A dermoscopic image of a skin lesion.
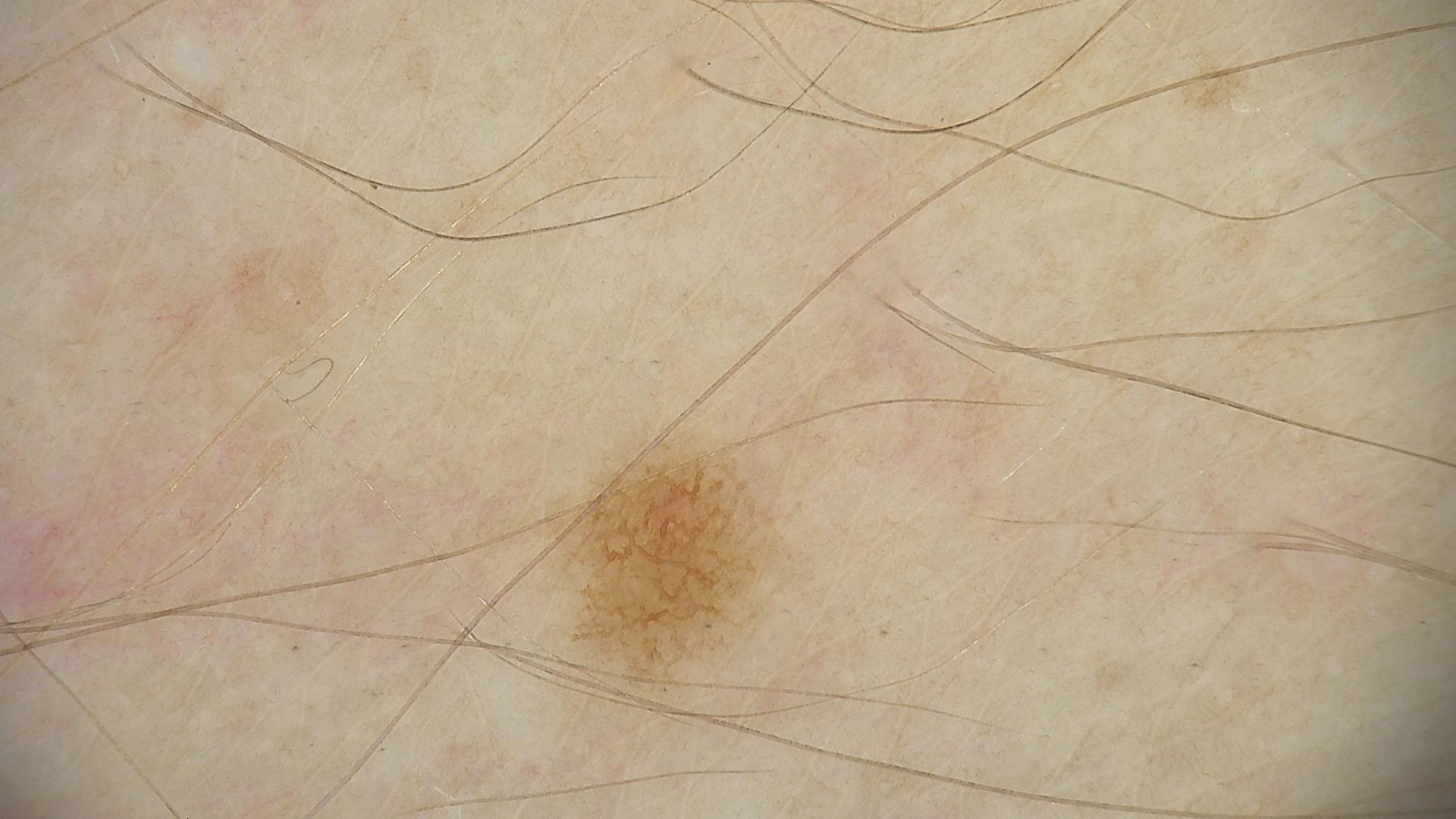category: banal
diagnostic label: junctional nevus (expert consensus)